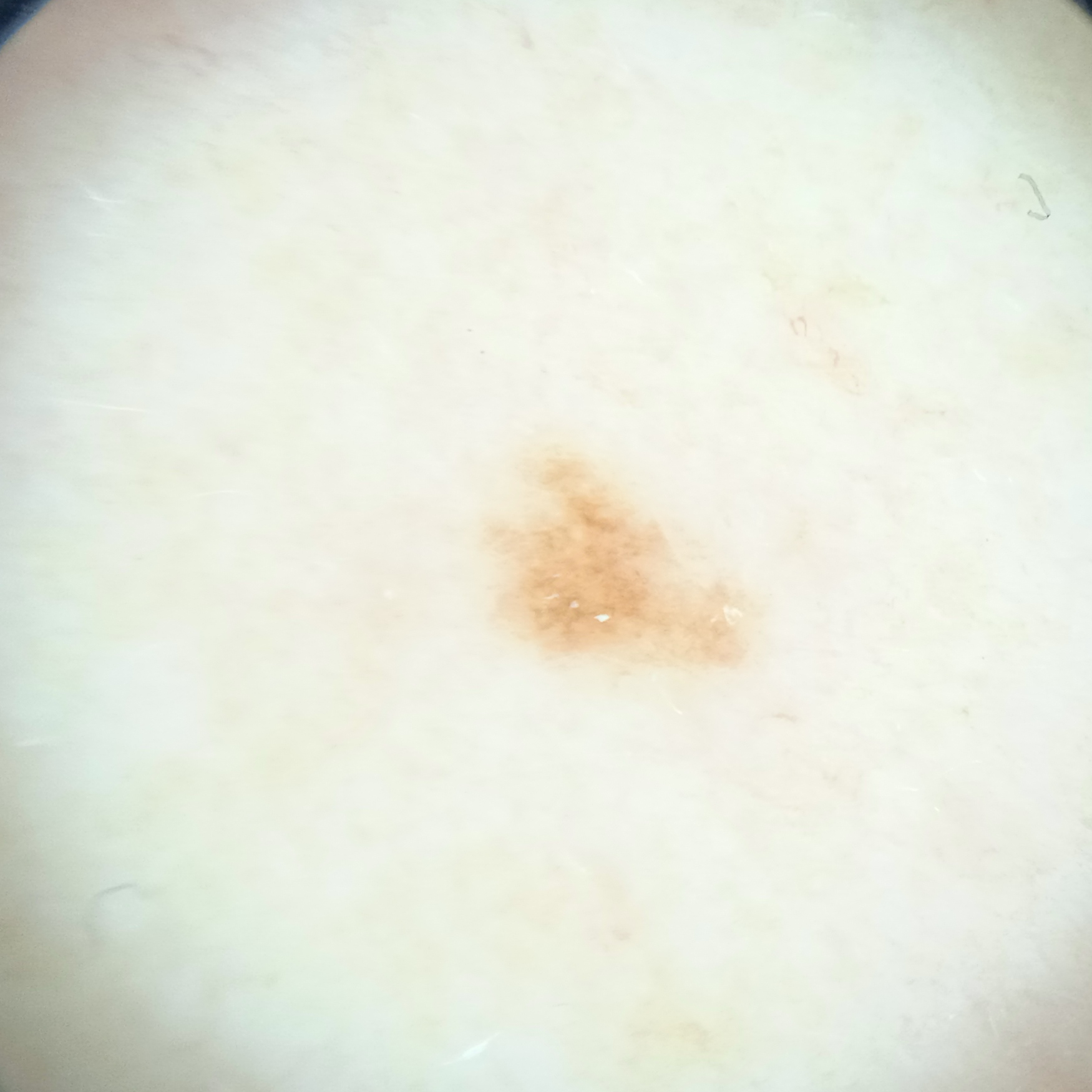A dermoscopy image of a skin lesion. A female subject 48 years of age. The lesion is located on the back. The diagnostic impression was a melanocytic nevus.